The affected area is the front of the torso, head or neck, arm and back of the hand · close-up view:
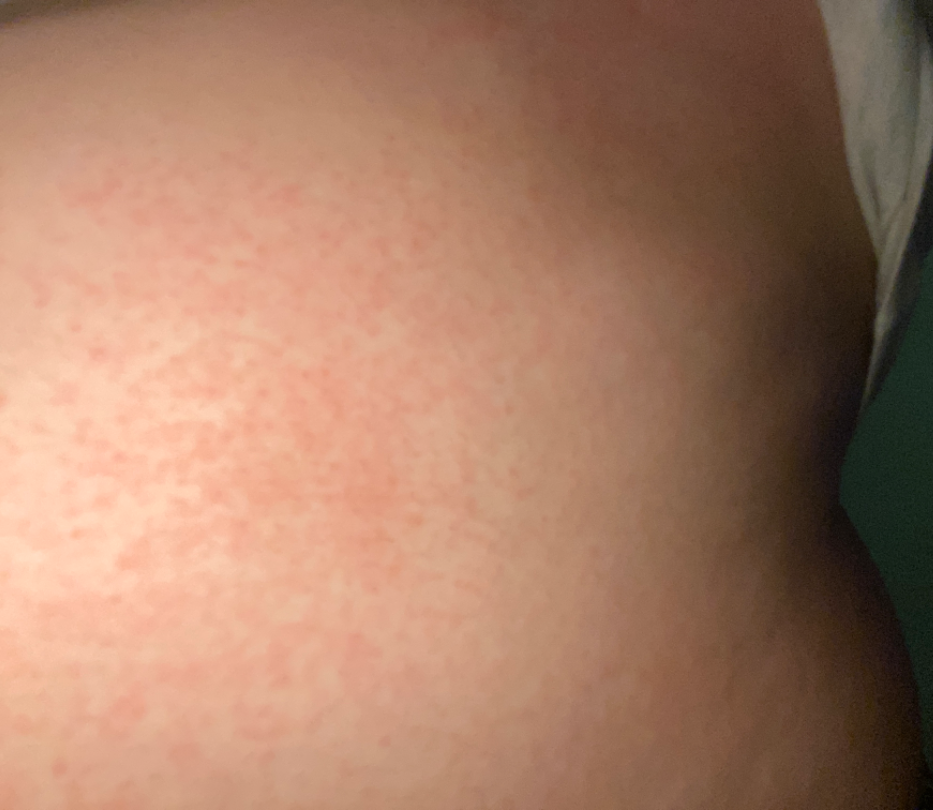Findings:
* assessment · indeterminate
* systemic symptoms · mouth sores
* onset · less than one week
* lesion symptoms · itching
* surface texture · fluid-filled, rough or flaky and raised or bumpy
* patient describes the issue as · a rash